The lesion is described as rough or flaky. Fitzpatrick I; human graders estimated MST 2 or 3. The photograph was taken at a distance:
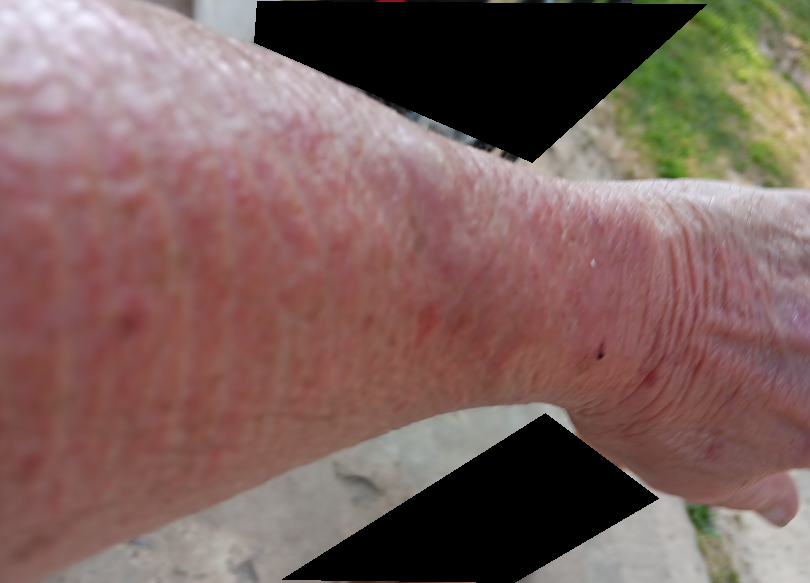<report>
<differential>
  <leading>SCC/SCCIS</leading>
</differential>
</report>